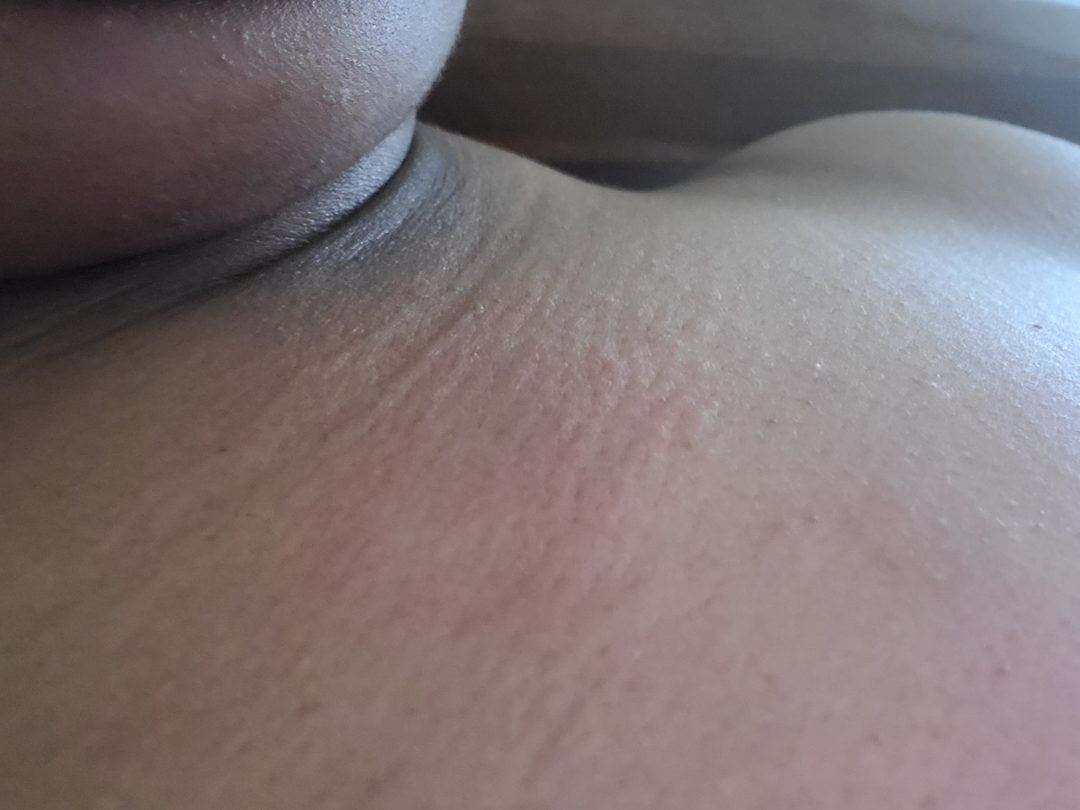Female subject, age 50–59. The patient described the issue as a rash. This image was taken at an angle. No relevant systemic symptoms. The reviewer's impression was Urticaria.